A male subject, aged around 70. A dermoscopic view of a skin lesion: 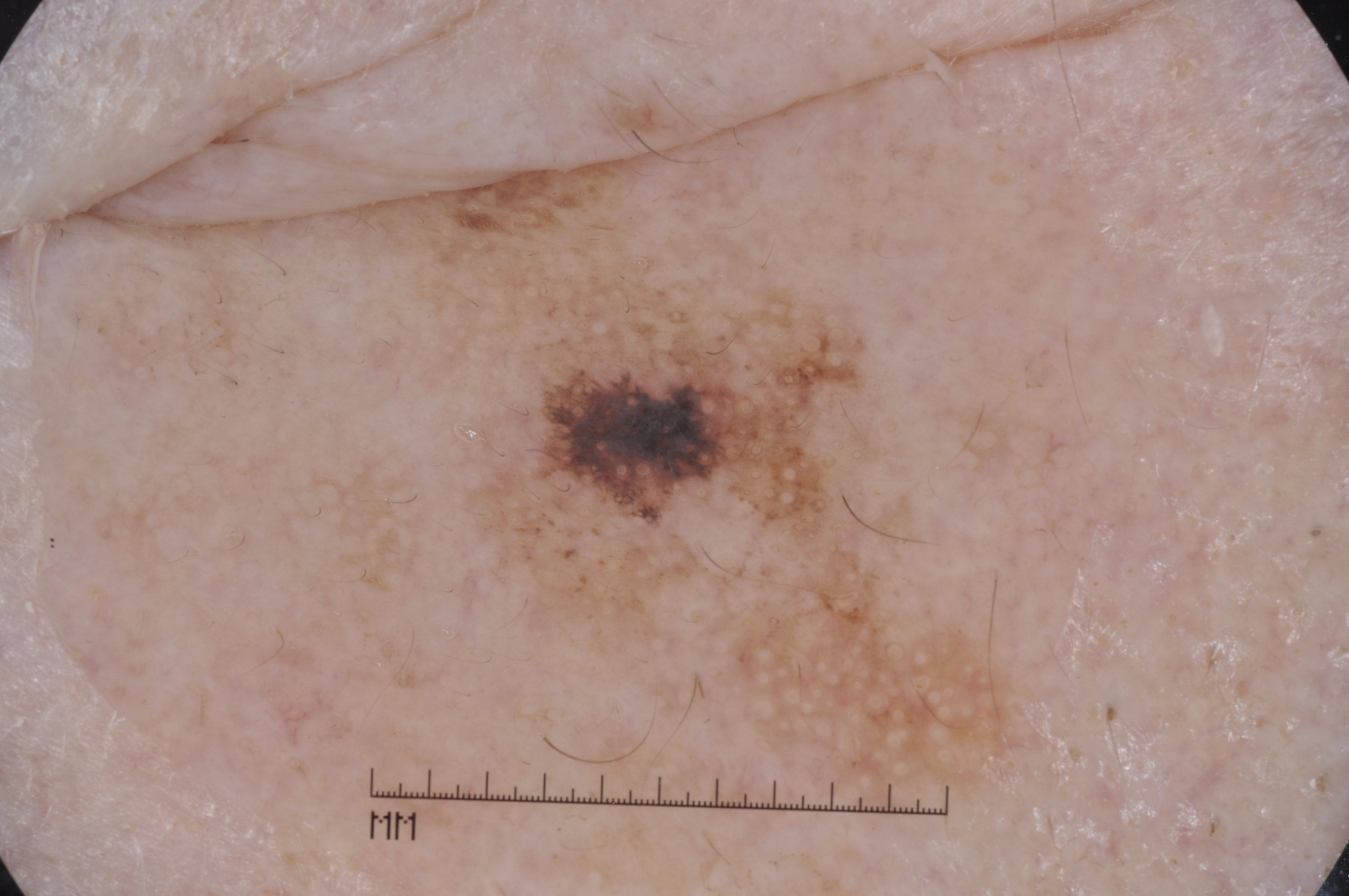Image and clinical context: On dermoscopy, the lesion shows no milia-like cysts, pigment network, streaks, or negative network. The lesion is bounded by 369, 160, 1035, 815. Diagnosis: Histopathologically confirmed as a melanoma, a malignant lesion.